A dermoscopic photograph of a skin lesion.
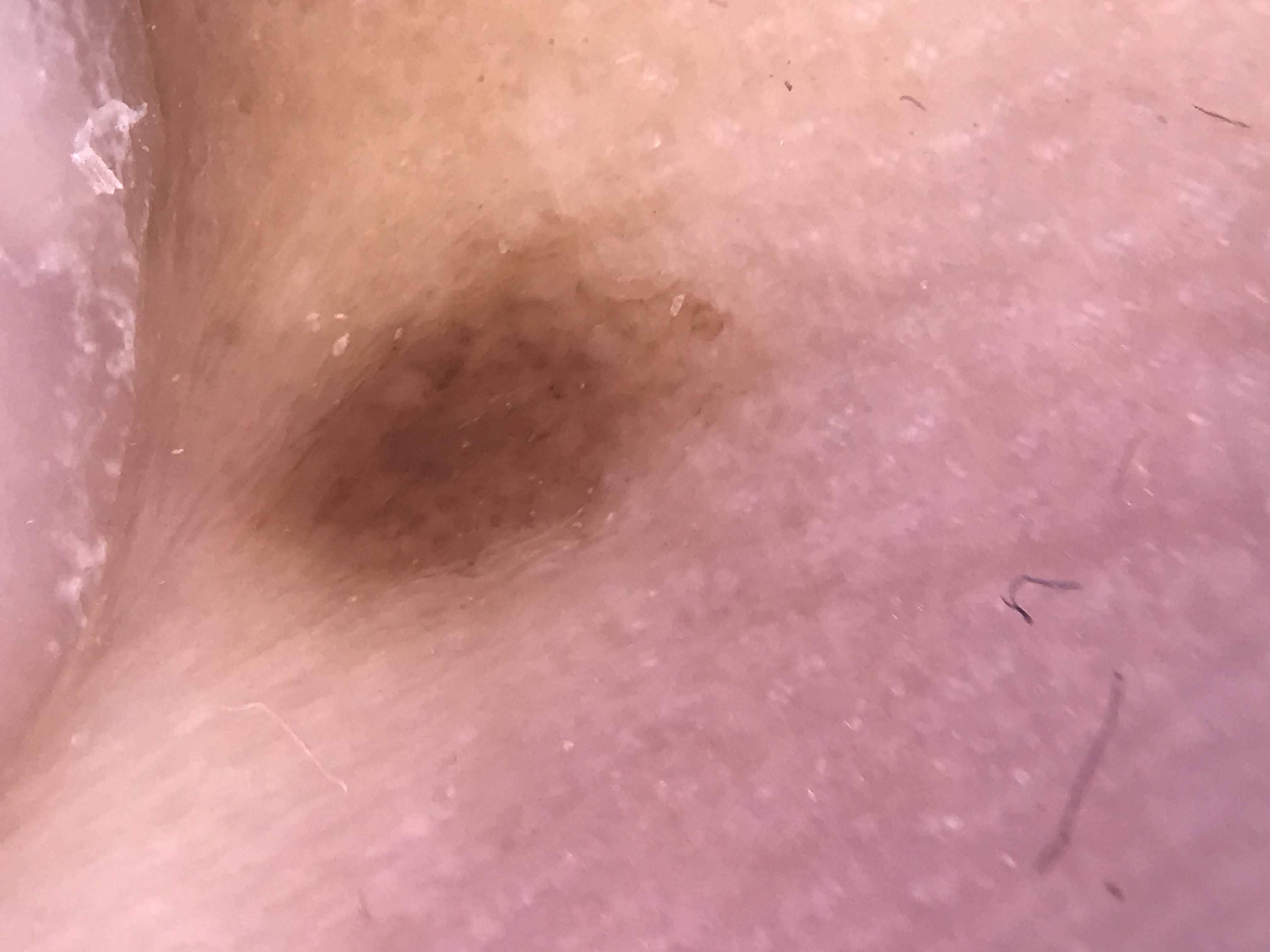{
  "diagnosis": {
    "name": "acral junctional nevus",
    "code": "ajb",
    "malignancy": "benign",
    "super_class": "melanocytic",
    "confirmation": "expert consensus"
  }
}